The photograph is a close-up of the affected area: 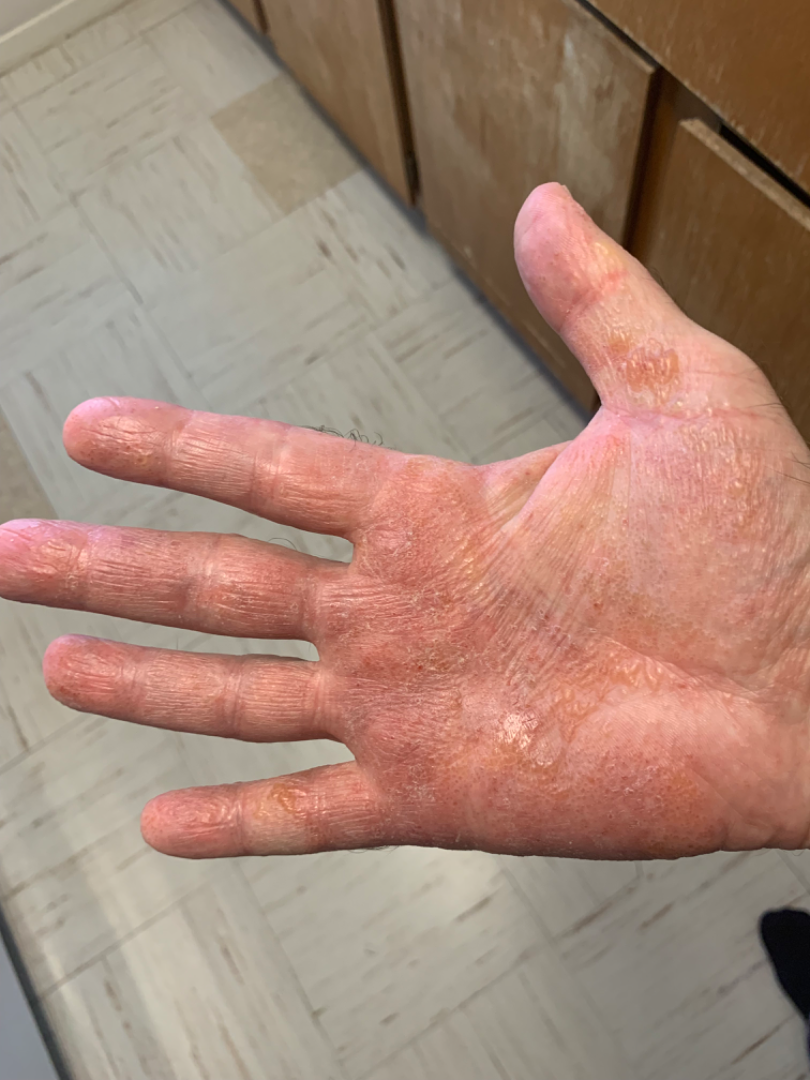Most consistent with Eczema; possibly Irritant Contact Dermatitis.